The patient is 50–59, female. Located on the sole of the foot and leg. A close-up photograph:
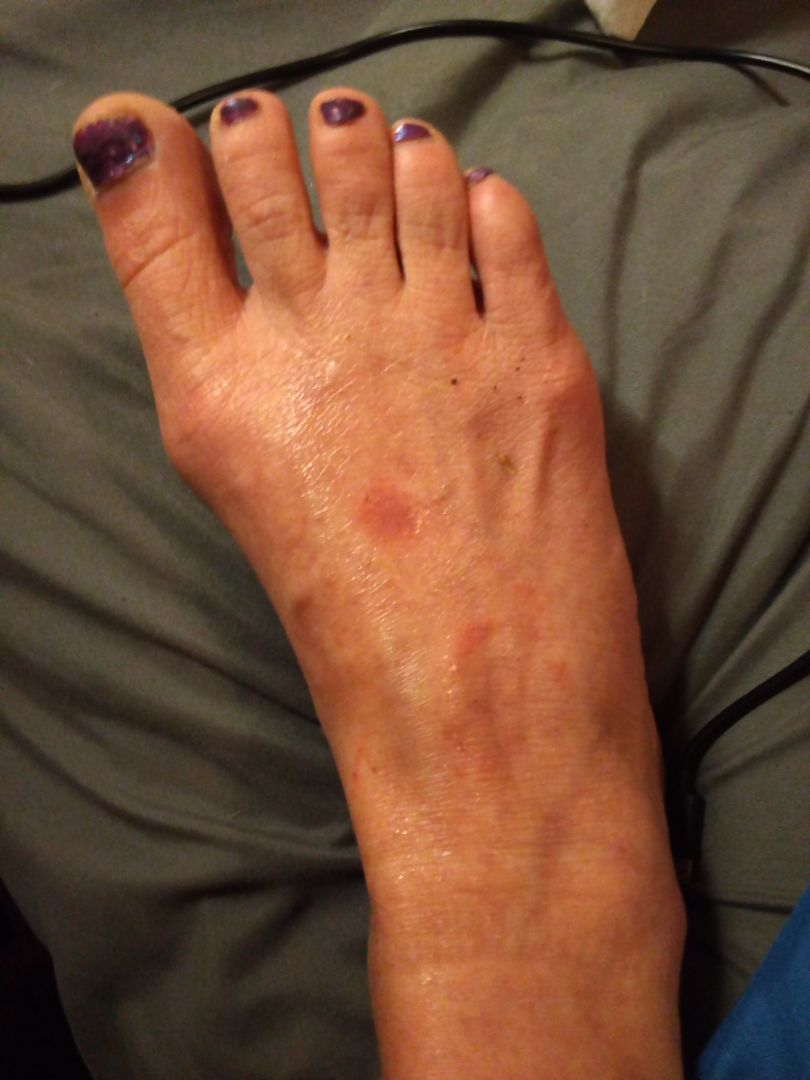<dermatology_case>
  <assessment>not assessable</assessment>
</dermatology_case>